The contributor is 18–29, male. The photo was captured at an angle. The lesion involves the arm and palm.
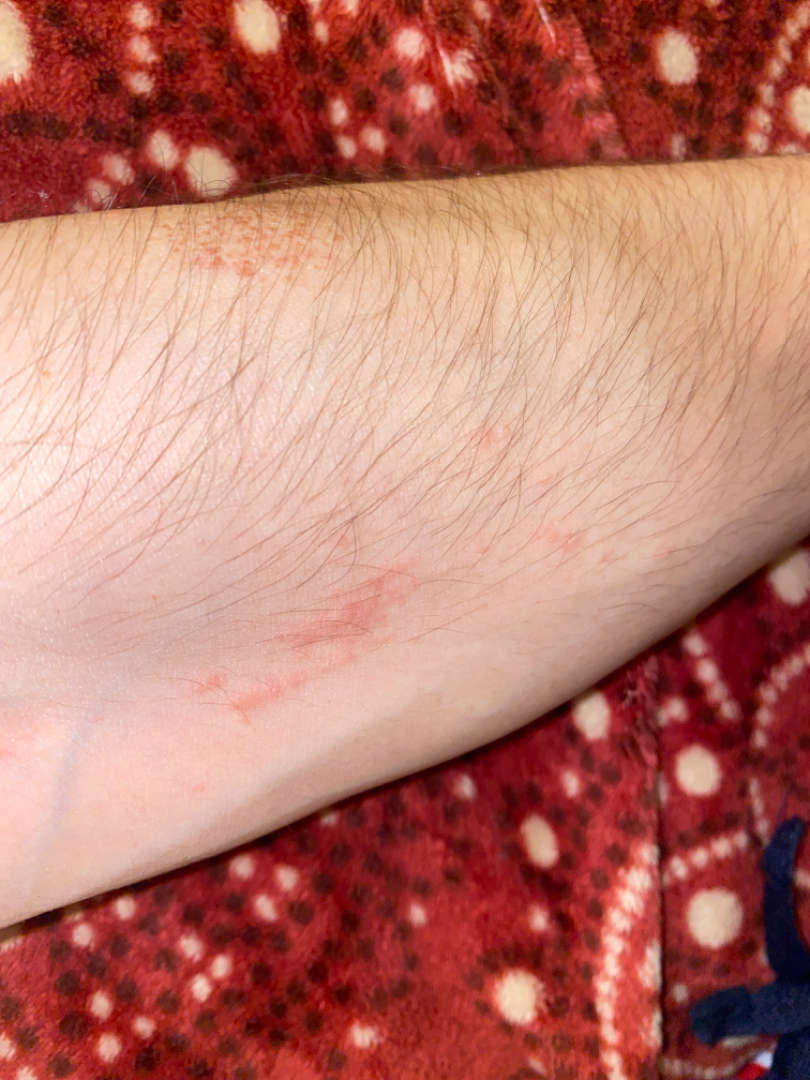The contributor reports itching.
The lesion is described as fluid-filled and raised or bumpy.
On dermatologist assessment of the image: the primary impression is Allergic Contact Dermatitis.